Male contributor, age 50–59 · the affected area is the head or neck · close-up view:
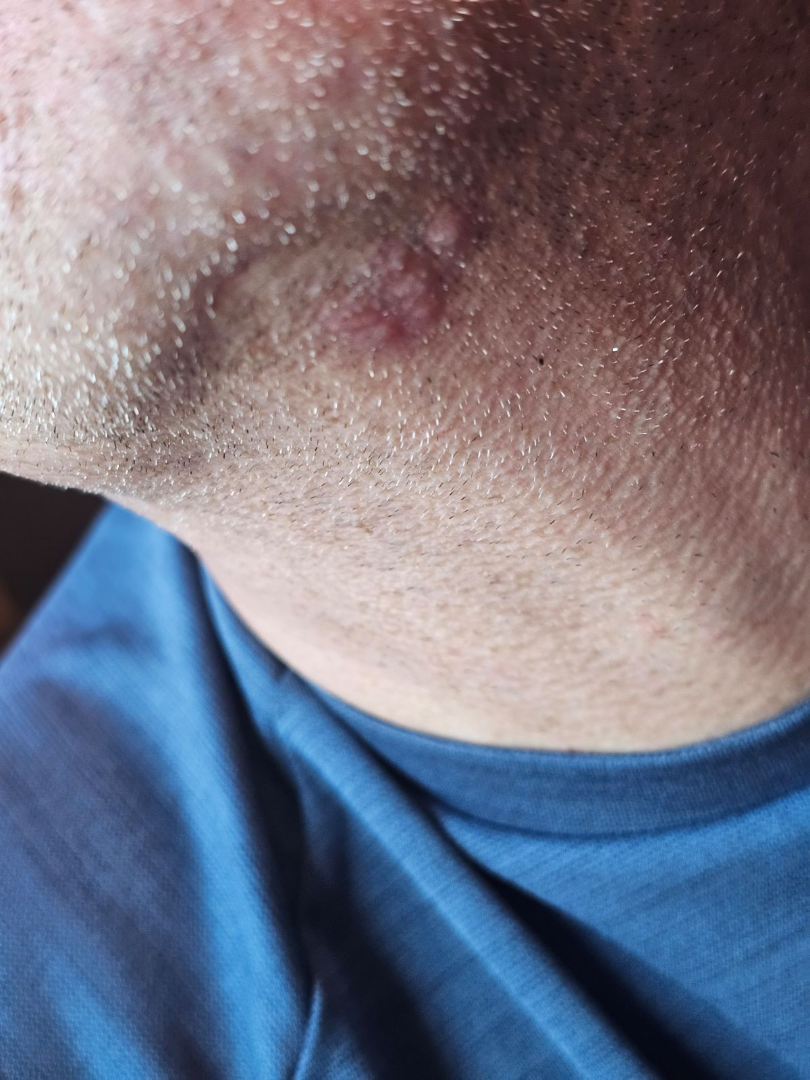Q: What is the dermatologist's impression?
A: Impetigo (considered); Herpes Simplex (considered)